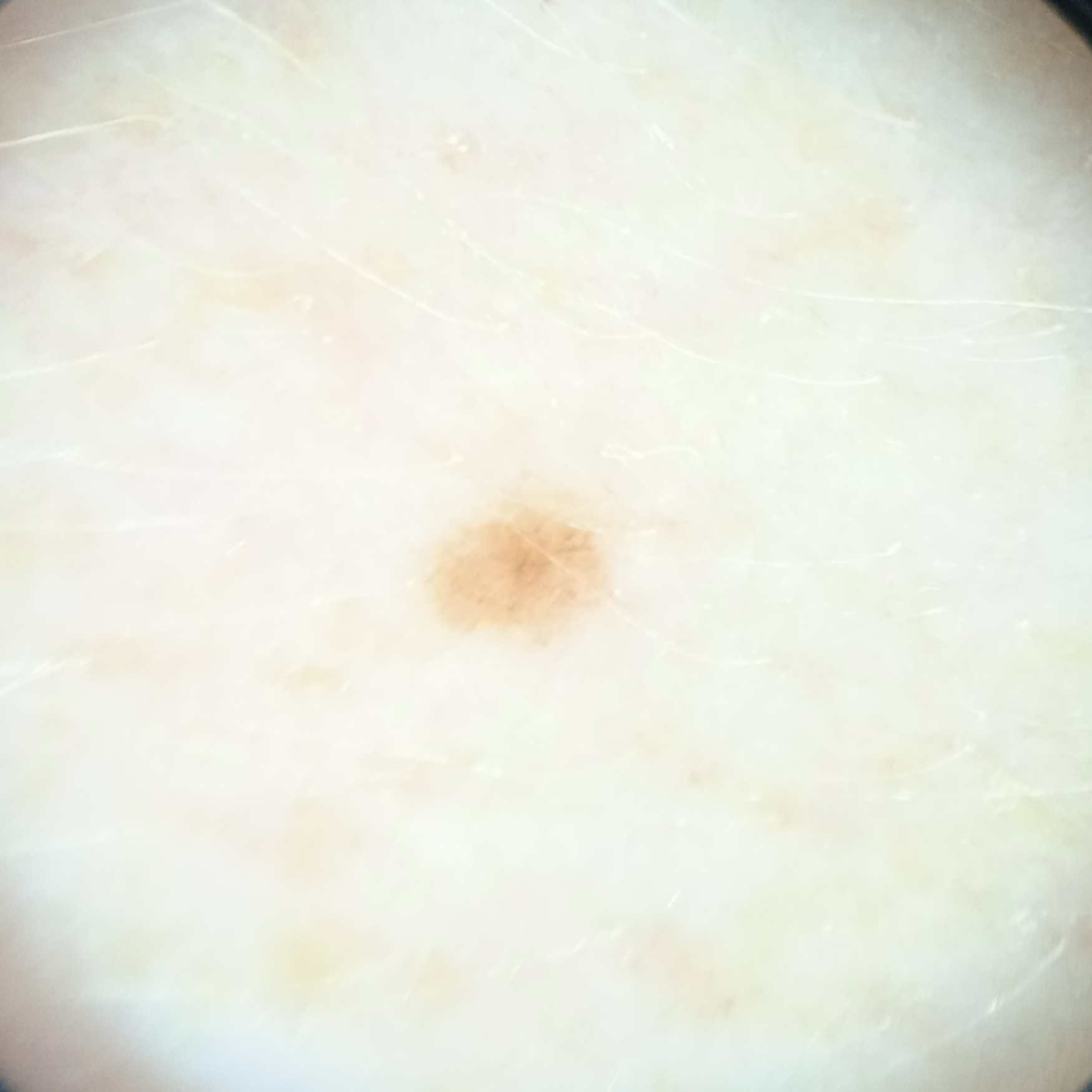{
  "image": "dermatoscopic image",
  "referral": "research study (no referral diagnosis)",
  "patient": {
    "age": 50,
    "sex": "female"
  },
  "sun_reaction": "skin reddens painfully with sun exposure",
  "lesion_location": "an arm",
  "lesion_size": {
    "diameter_mm": 2.0
  },
  "diagnosis": {
    "name": "melanocytic nevus",
    "malignancy": "benign"
  }
}